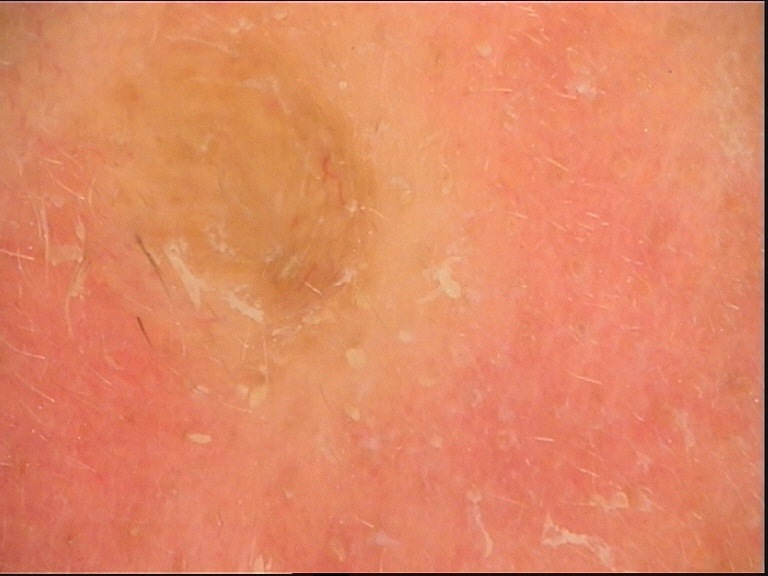Diagnosed as a seborrheic keratosis.